A female subject in their mid-60s.
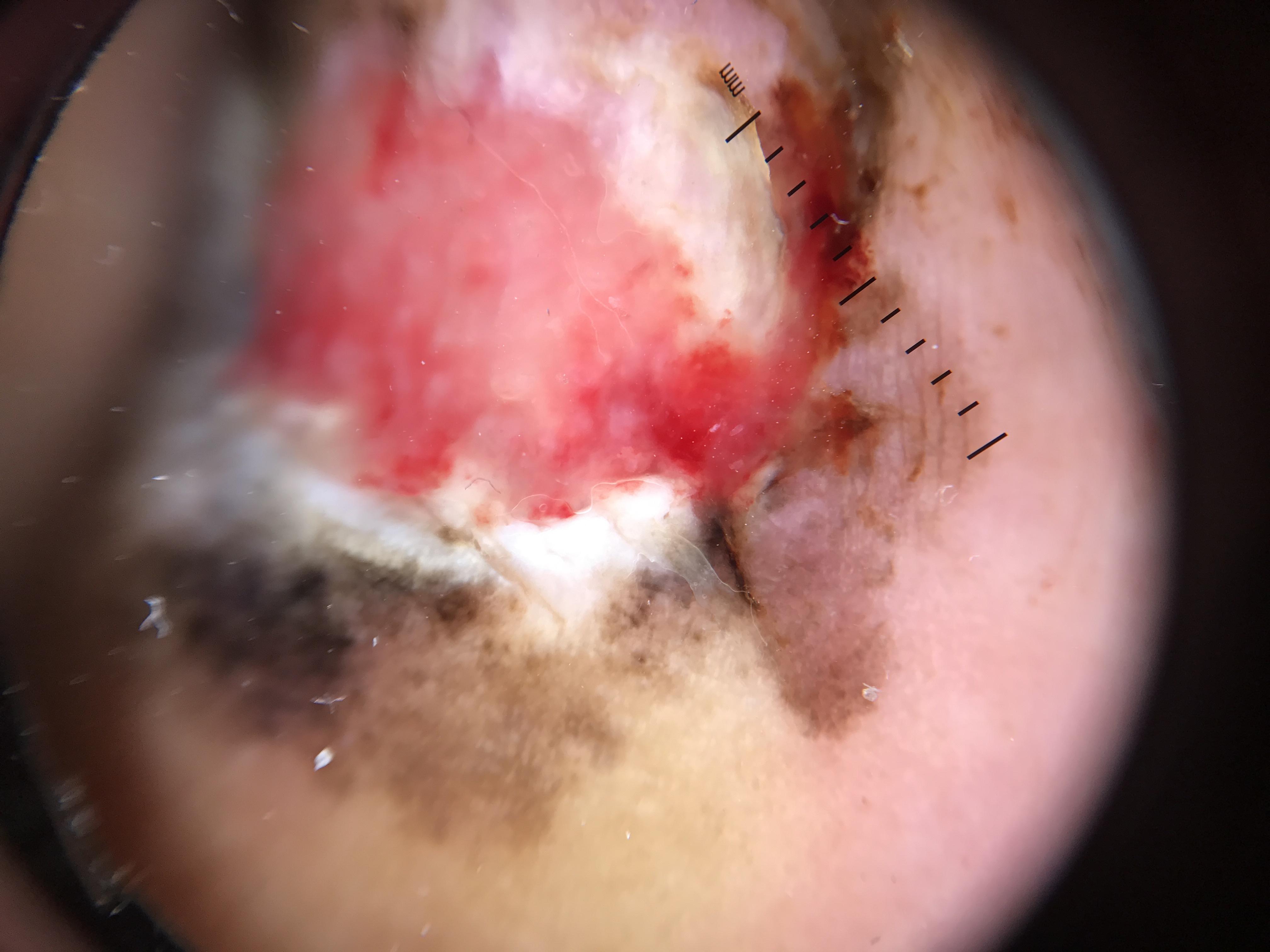Conclusion:
Histopathology confirmed a melanoma.